A patient in their early 40s: 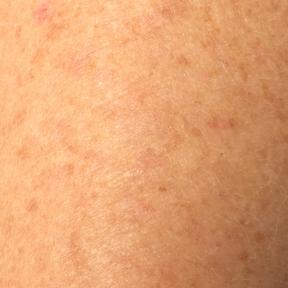The lesion involves a forearm. Diagnosed by dermatologist consensus as an actinic keratosis.